A dermatoscopic image of a skin lesion.
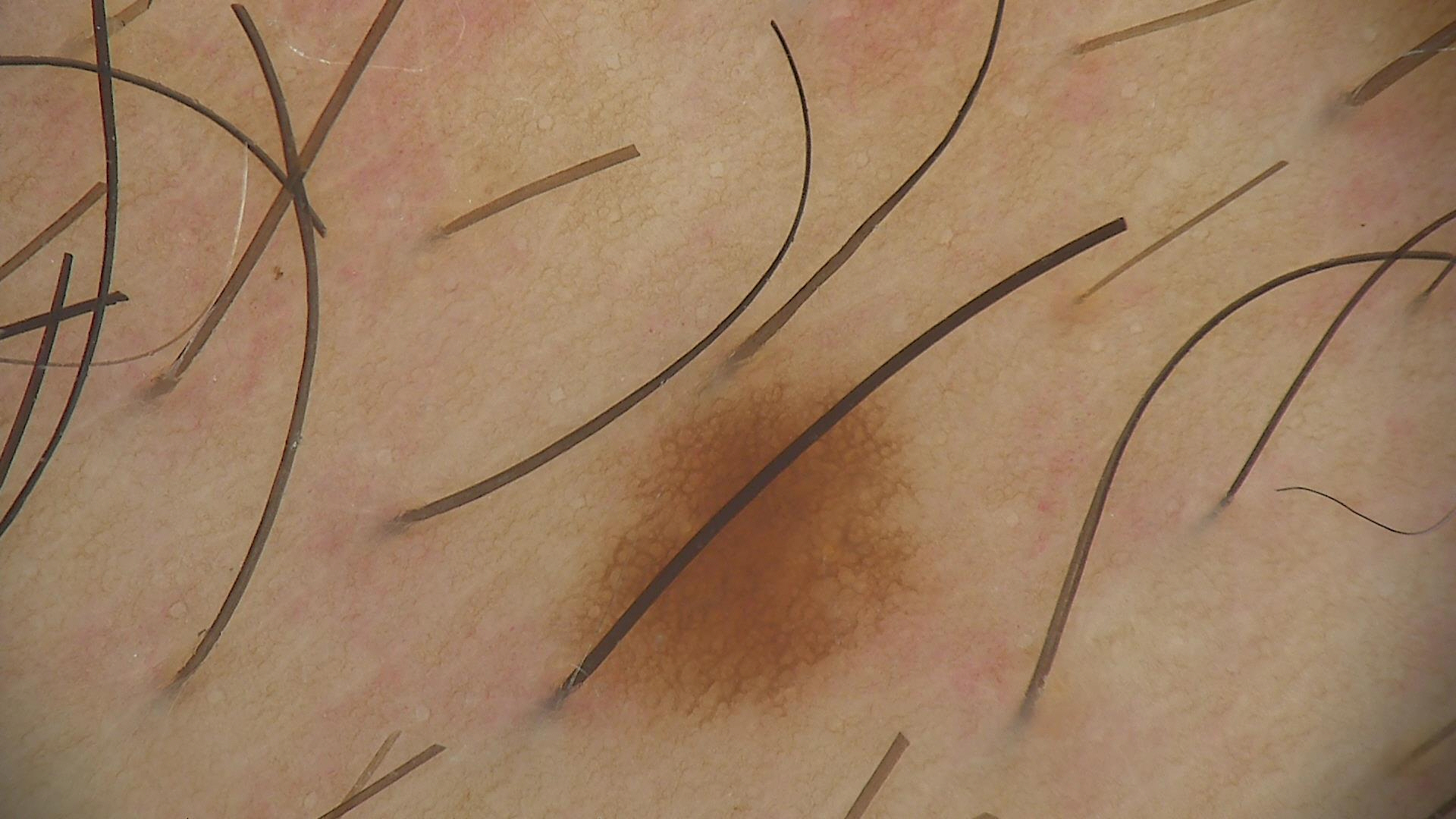The diagnostic label was a junctional nevus.